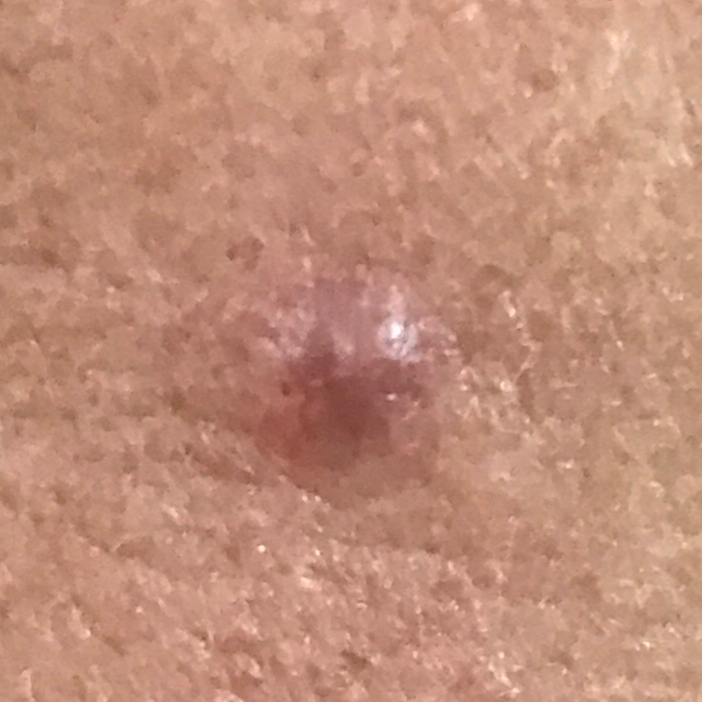image: smartphone clinical photo
subject: male, in their 50s
Fitzpatrick: II
location: the face
reported symptoms: elevation
pathology: basal cell carcinoma (biopsy-proven)